A dermoscopy image of a single skin lesion: 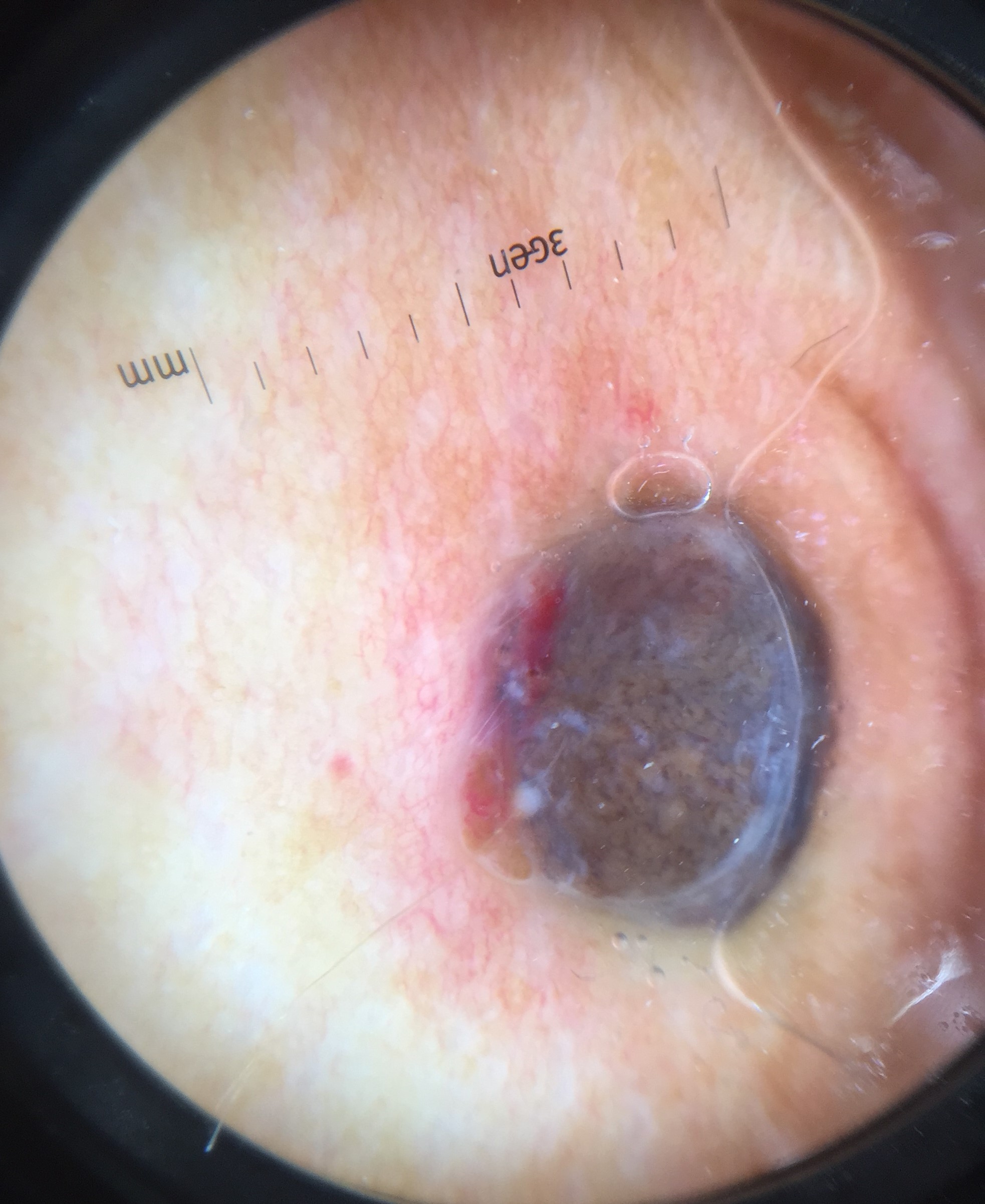label: melanoma (biopsy-proven).